The patient reports associated fatigue; the patient described the issue as a rash; the lesion is described as raised or bumpy; the subject is a female aged 40–49; the affected area is the head or neck, front of the torso, arm and back of the torso; present for less than one week; the photograph was taken at a distance; the patient reports itching: 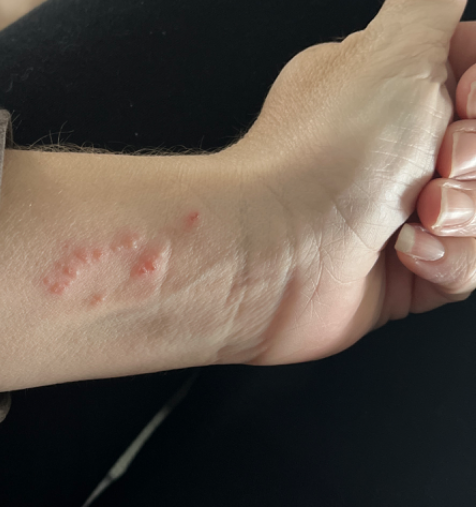Findings: The case was difficult to assess from the available photograph.